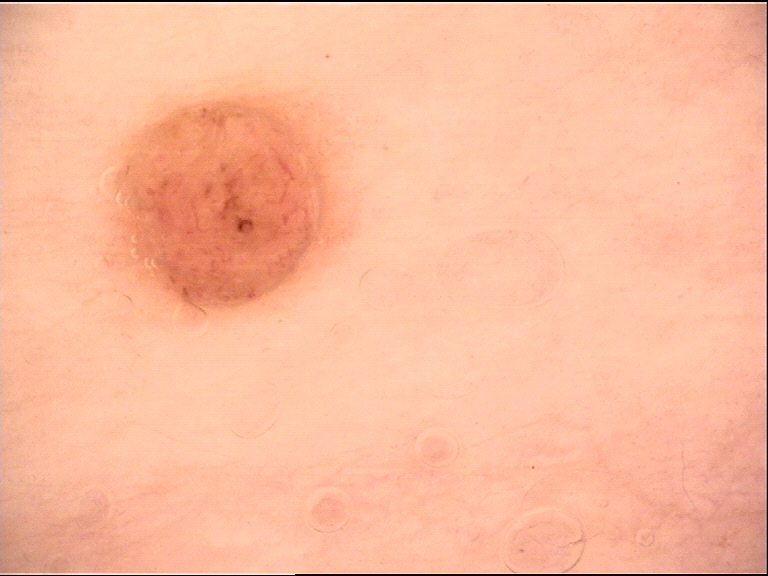Case:
- label: dermal nevus (expert consensus)